This image was taken at a distance, skin tone: Fitzpatrick IV; non-clinician graders estimated Monk Skin Tone 4 (US pool) or 2 (India pool), located on the head or neck, the lesion is described as raised or bumpy, symptoms reported: bothersome appearance, the patient considered this a hair problem.
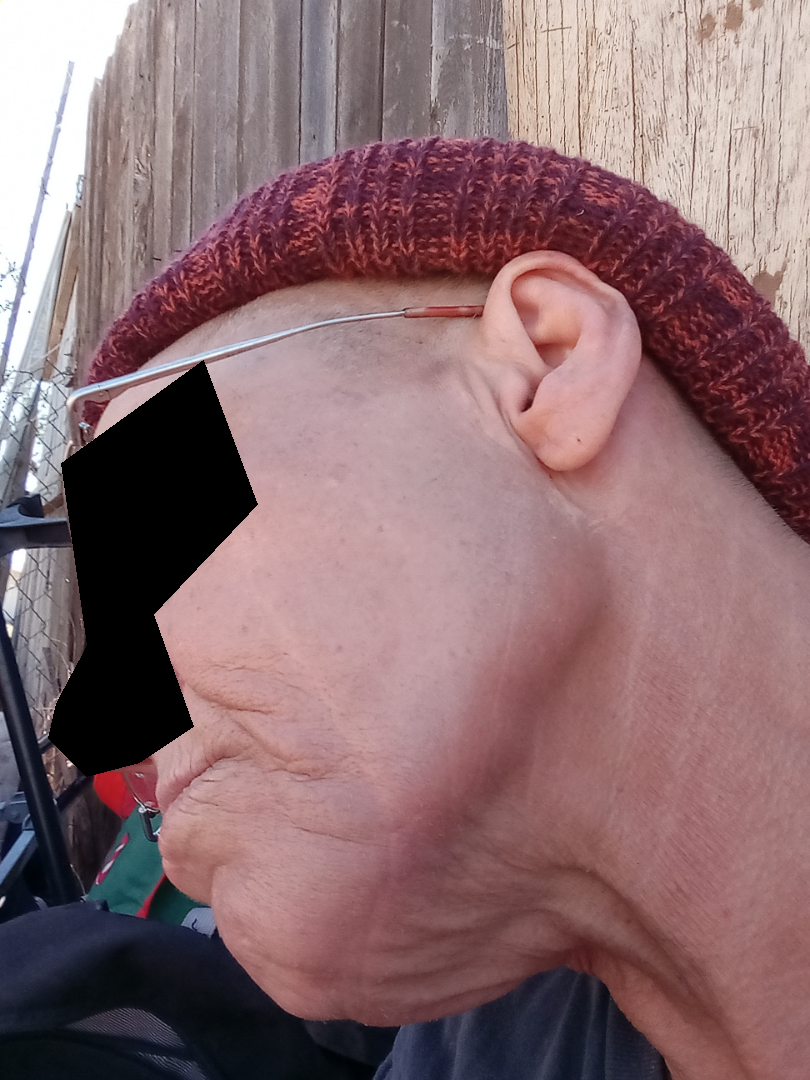  assessment: none discernible